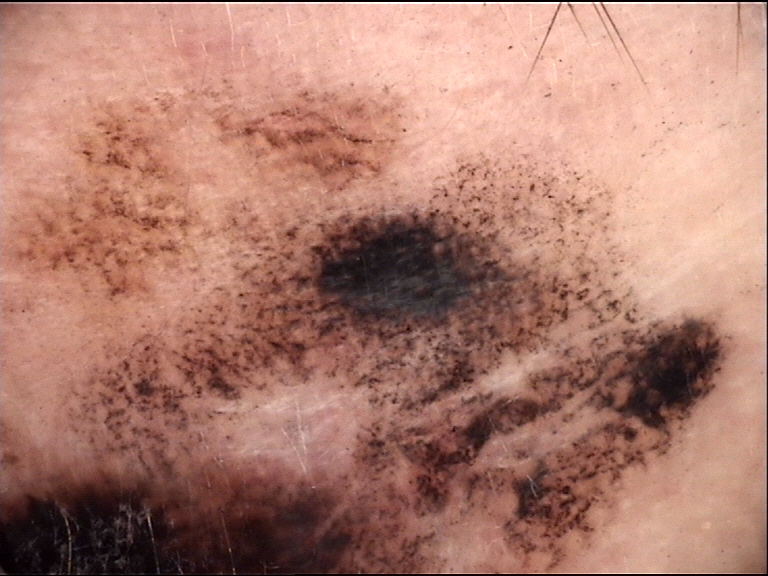{"image": "dermatoscopy", "diagnosis": {"name": "lentigo maligna", "code": "lm", "malignancy": "malignant", "super_class": "melanocytic", "confirmation": "histopathology"}}